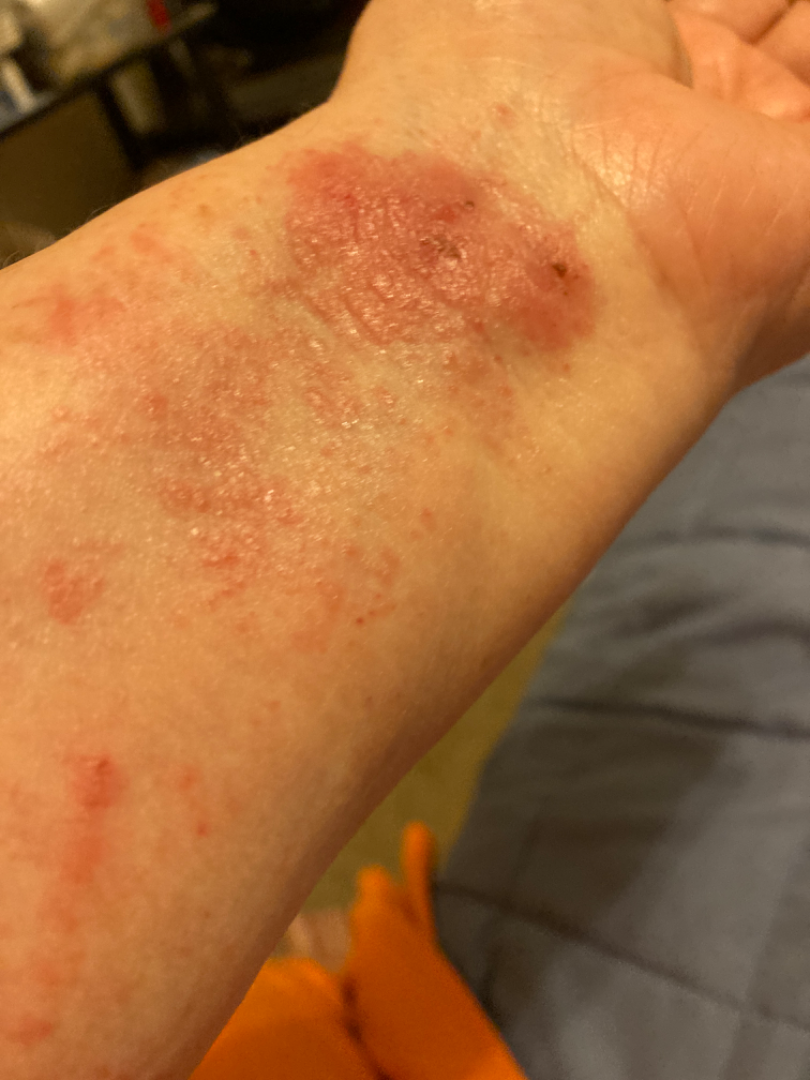An image taken at an angle. Located on the arm. Female subject, age 70–79. On photographic review: Allergic Contact Dermatitis (leading); Crusted eczematous dermatitis (considered); Eczema (considered); Secondary impetiginization (remote).